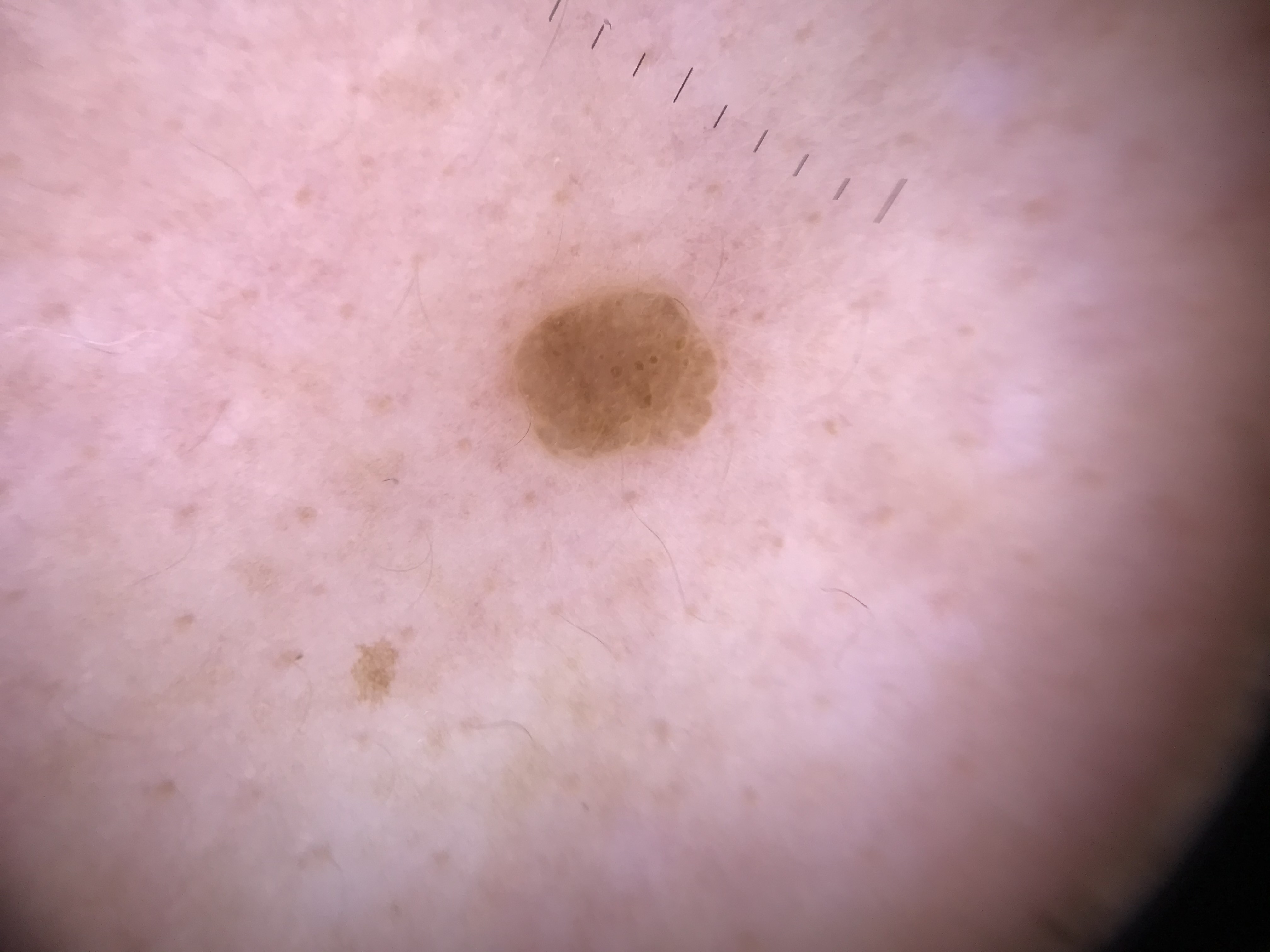image: dermoscopy
diagnosis:
  name: seborrheic keratosis
  code: sk
  malignancy: benign
  super_class: non-melanocytic
  confirmation: expert consensus